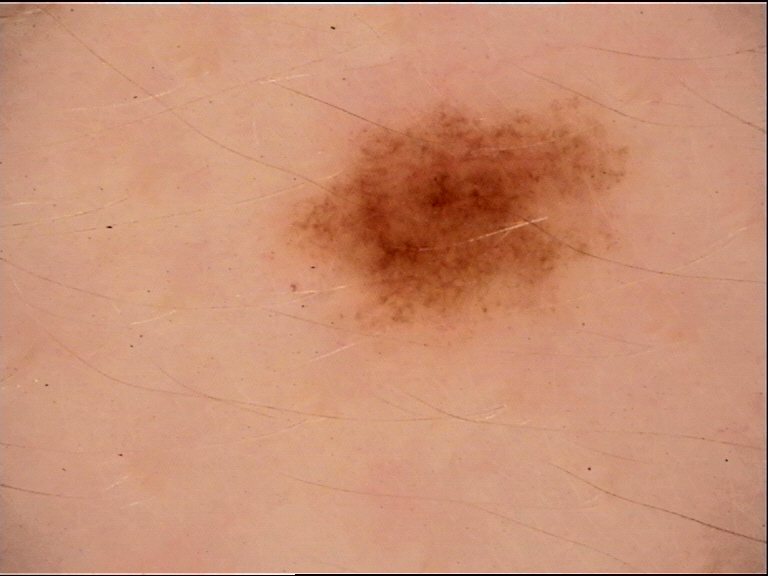A dermoscopy image of a single skin lesion. Classified as a dysplastic junctional nevus.